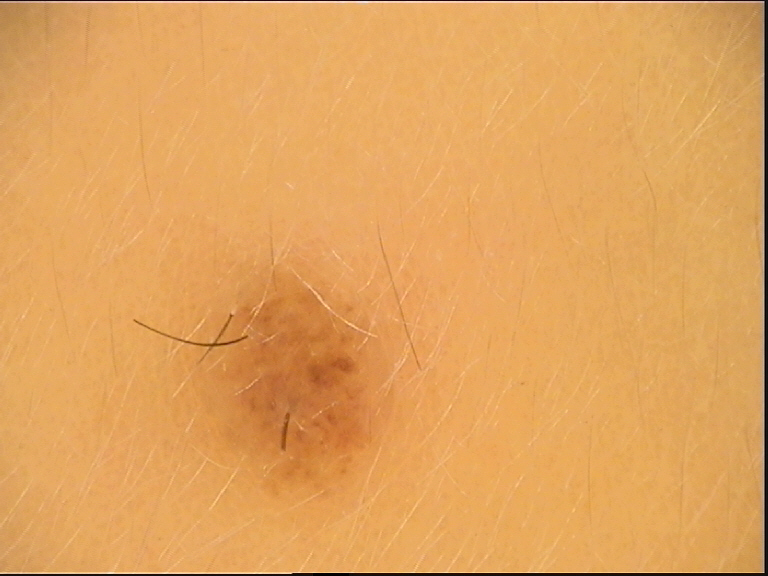The architecture is that of a banal lesion. The diagnosis was a compound nevus.